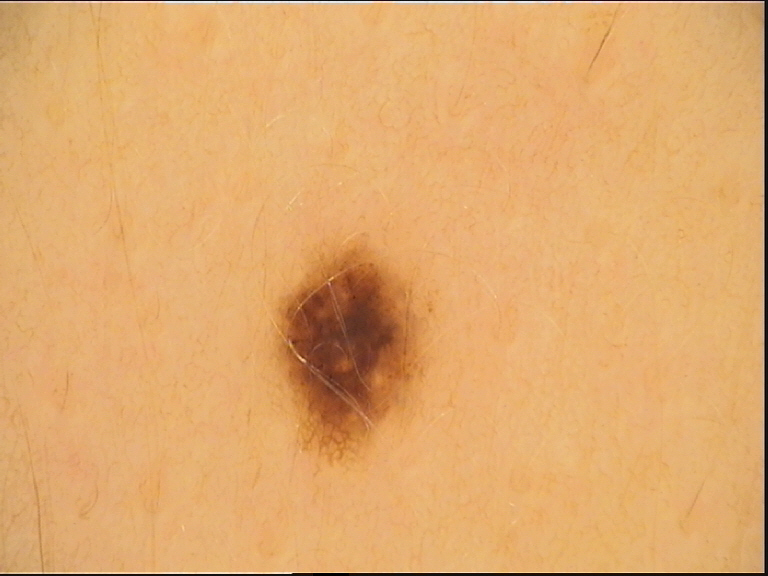assessment = dysplastic junctional nevus (expert consensus).